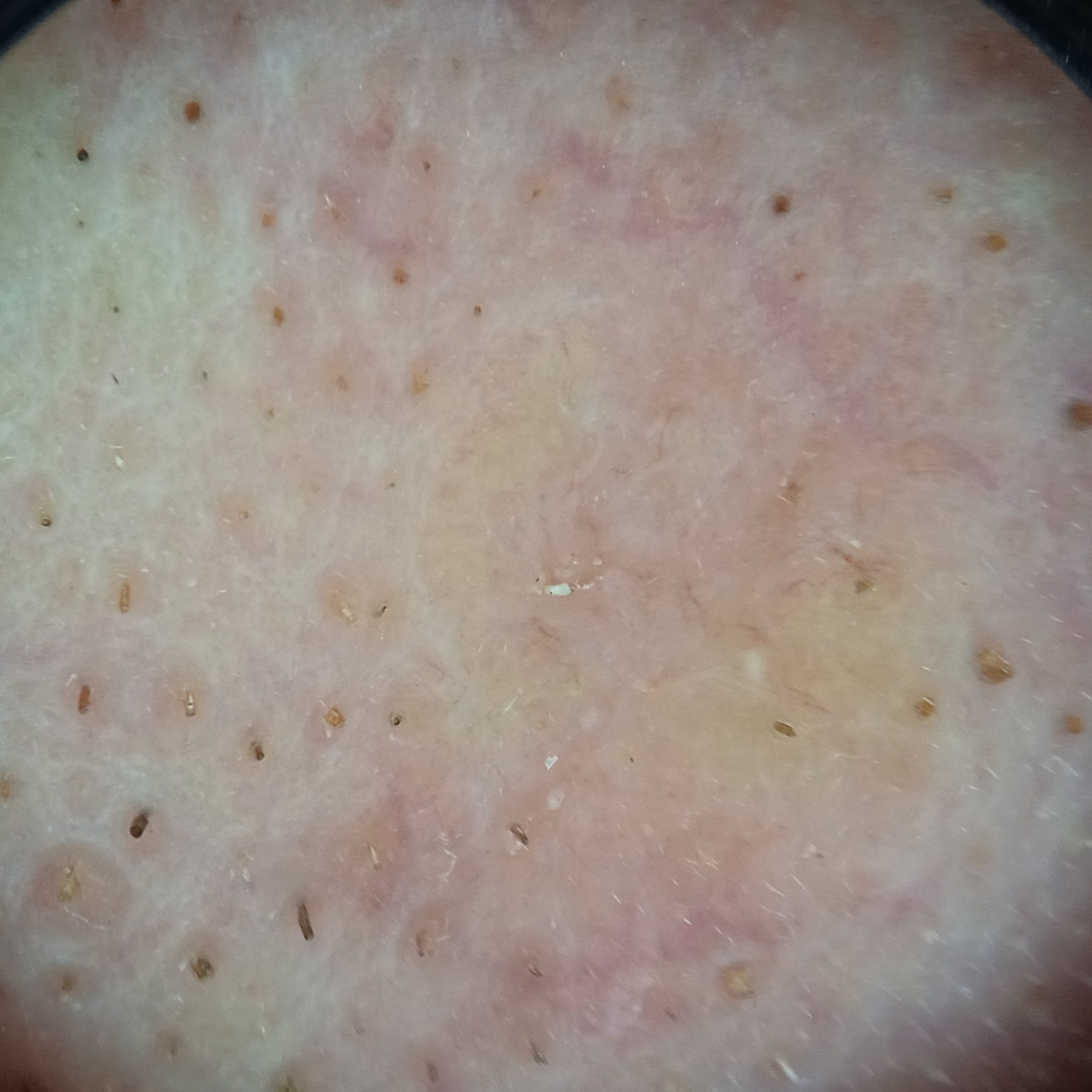A male patient age 60.
A dermoscopy image of a skin lesion.
The lesion is located on the face.
The lesion measures approximately 8.5 mm.
Histopathologically confirmed as a basal cell carcinoma, following excision, with a measured tumor thickness of 1.7 mm.